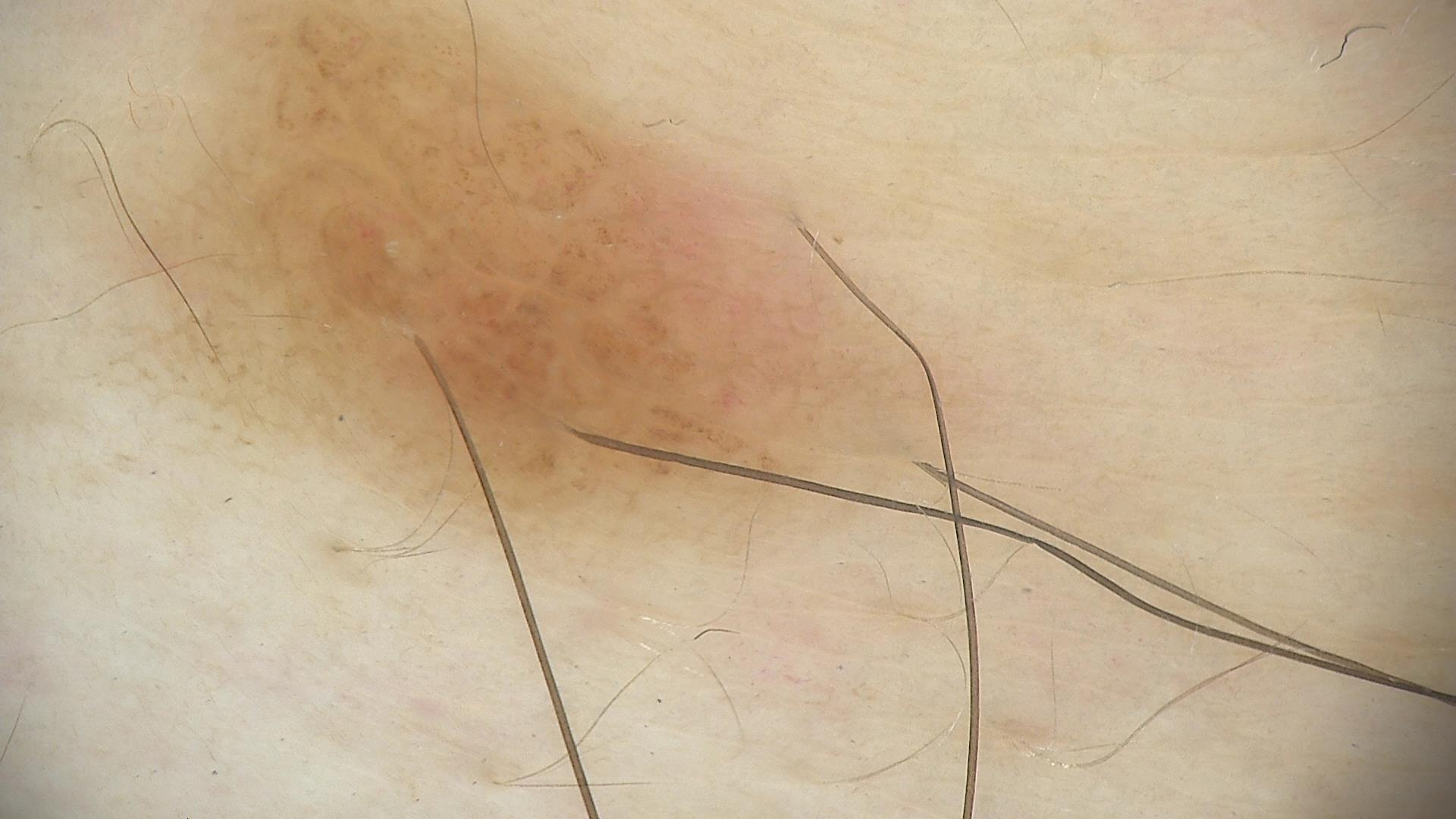The diagnosis was a dysplastic compound nevus.